The patient says their skin tans without first burning; the patient describes having few moles overall; a clinical photograph showing a skin lesion; acquired for a research image collection, with no referral diagnosis; by self-report, no sunbed use and no immunosuppression; a male subject age 79:
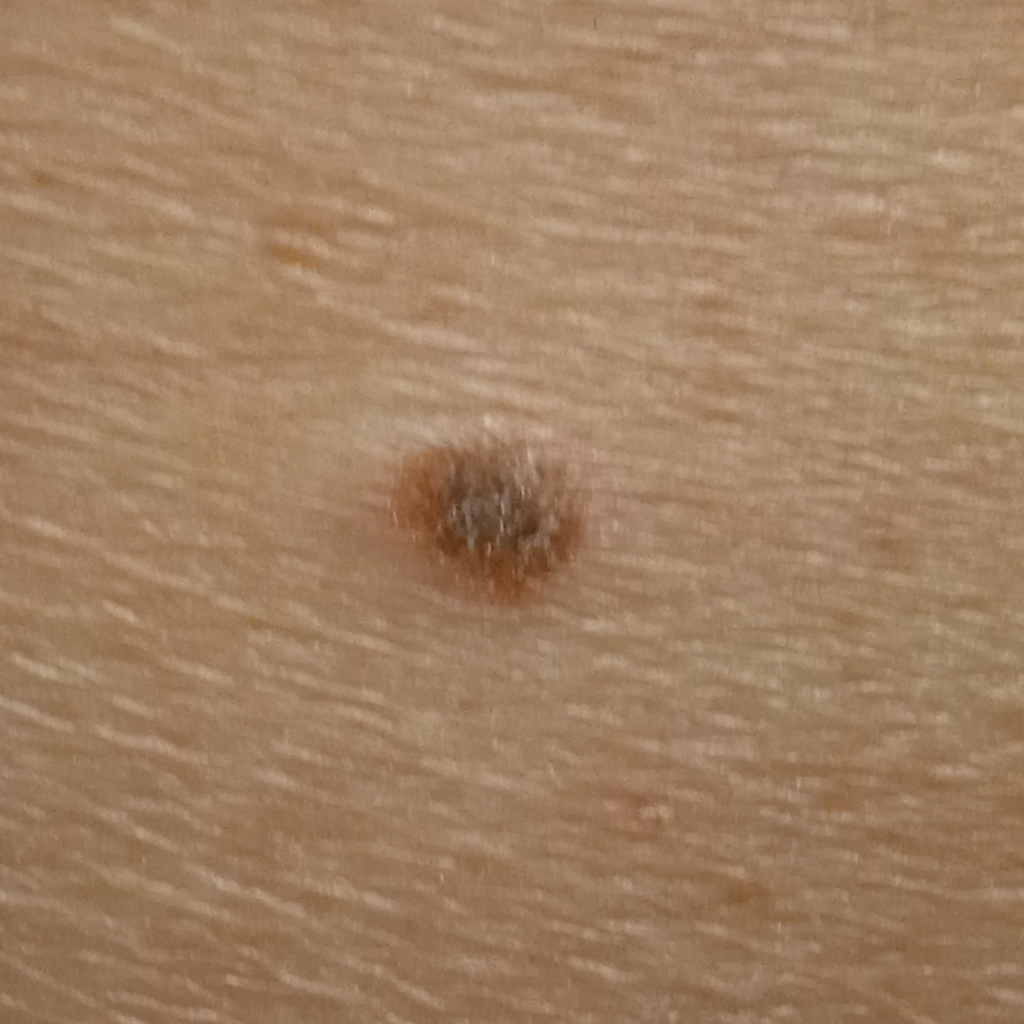Findings:
* lesion size: 5.9 mm
* assessment: seborrheic keratosis (dermatologist consensus)